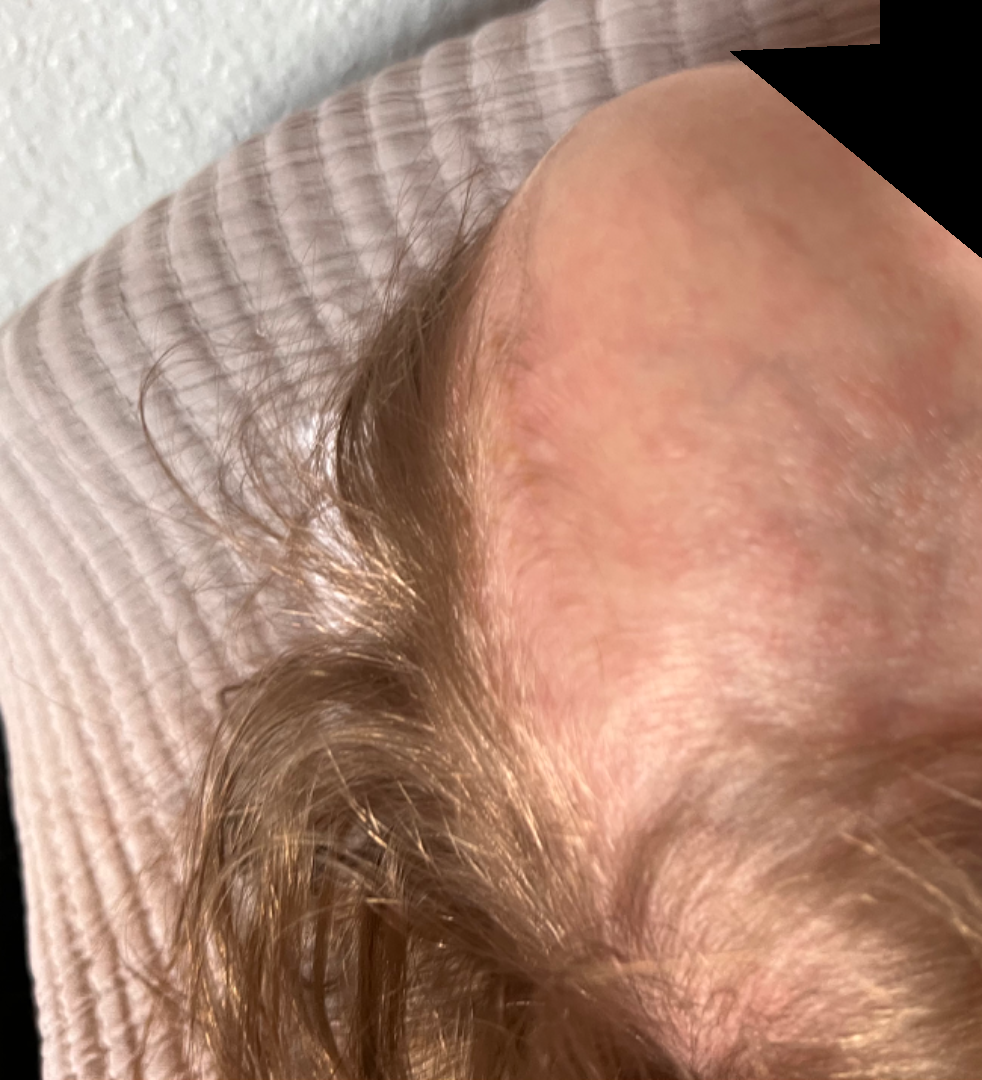The case was difficult to assess from the available photograph. A close-up photograph.